A dermoscopy image of a single skin lesion:
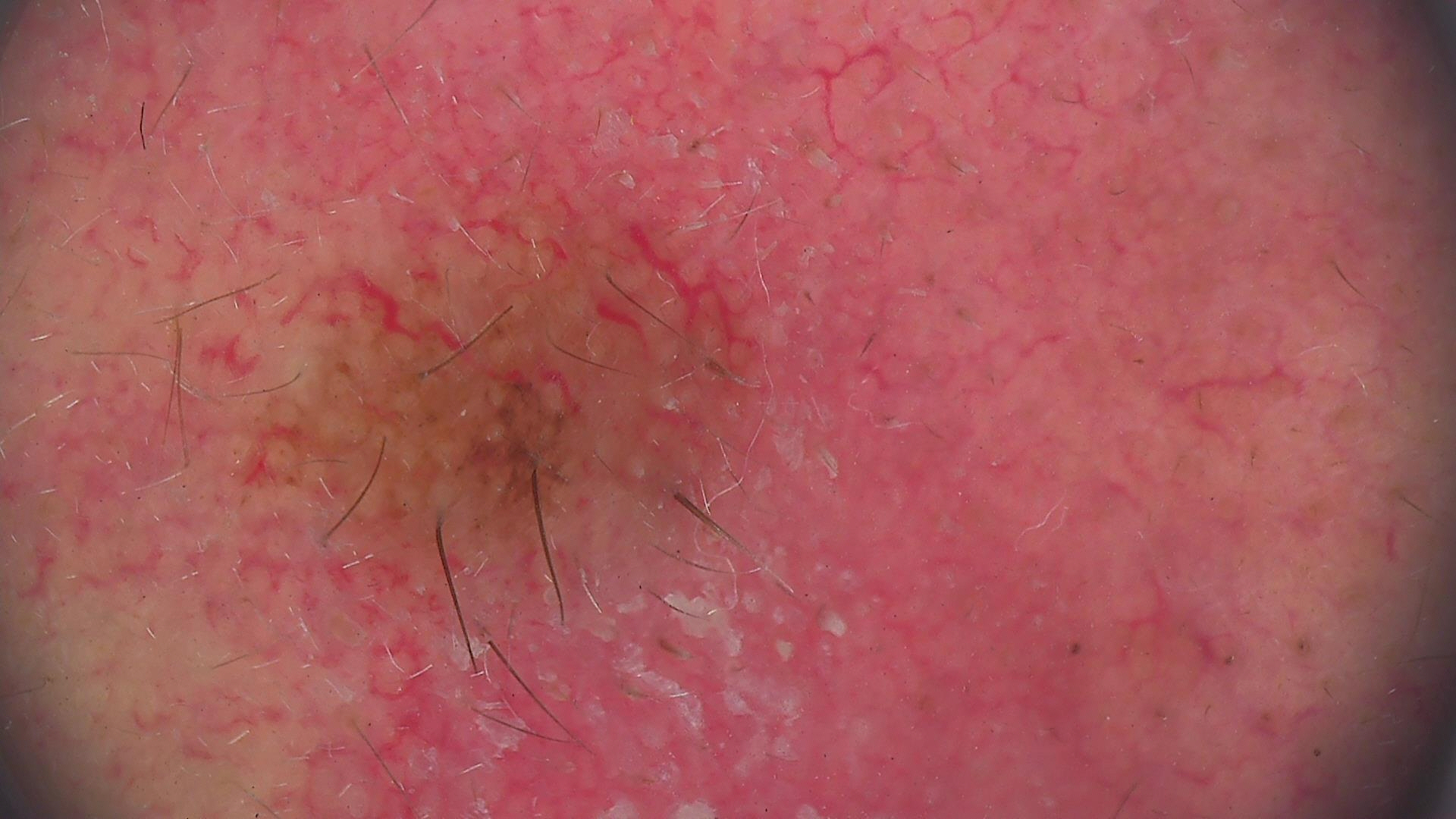category: banal; diagnostic label: compound nevus (expert consensus).